The contributor is 18–29, male. The lesion involves the leg. This is a close-up image:
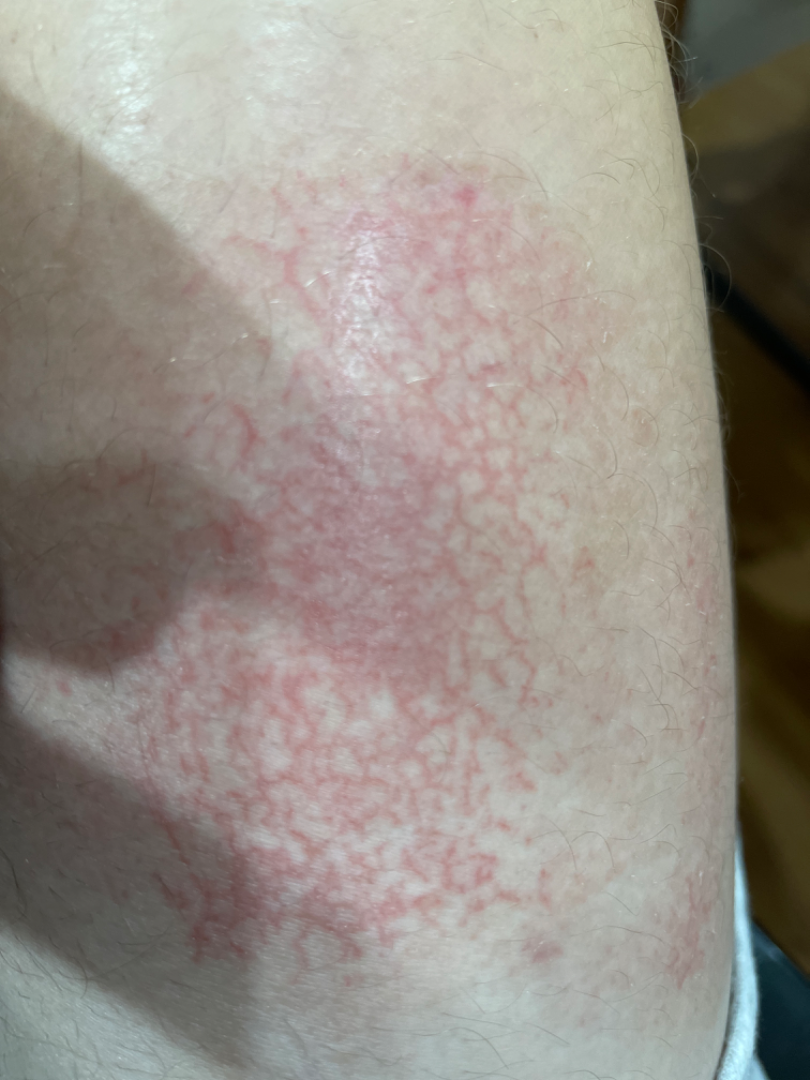- lesion texture · rough or flaky
- onset · less than one week
- patient describes the issue as · a rash
- symptoms · bothersome appearance, pain and burning
- diagnostic considerations · the primary impression is Eczema